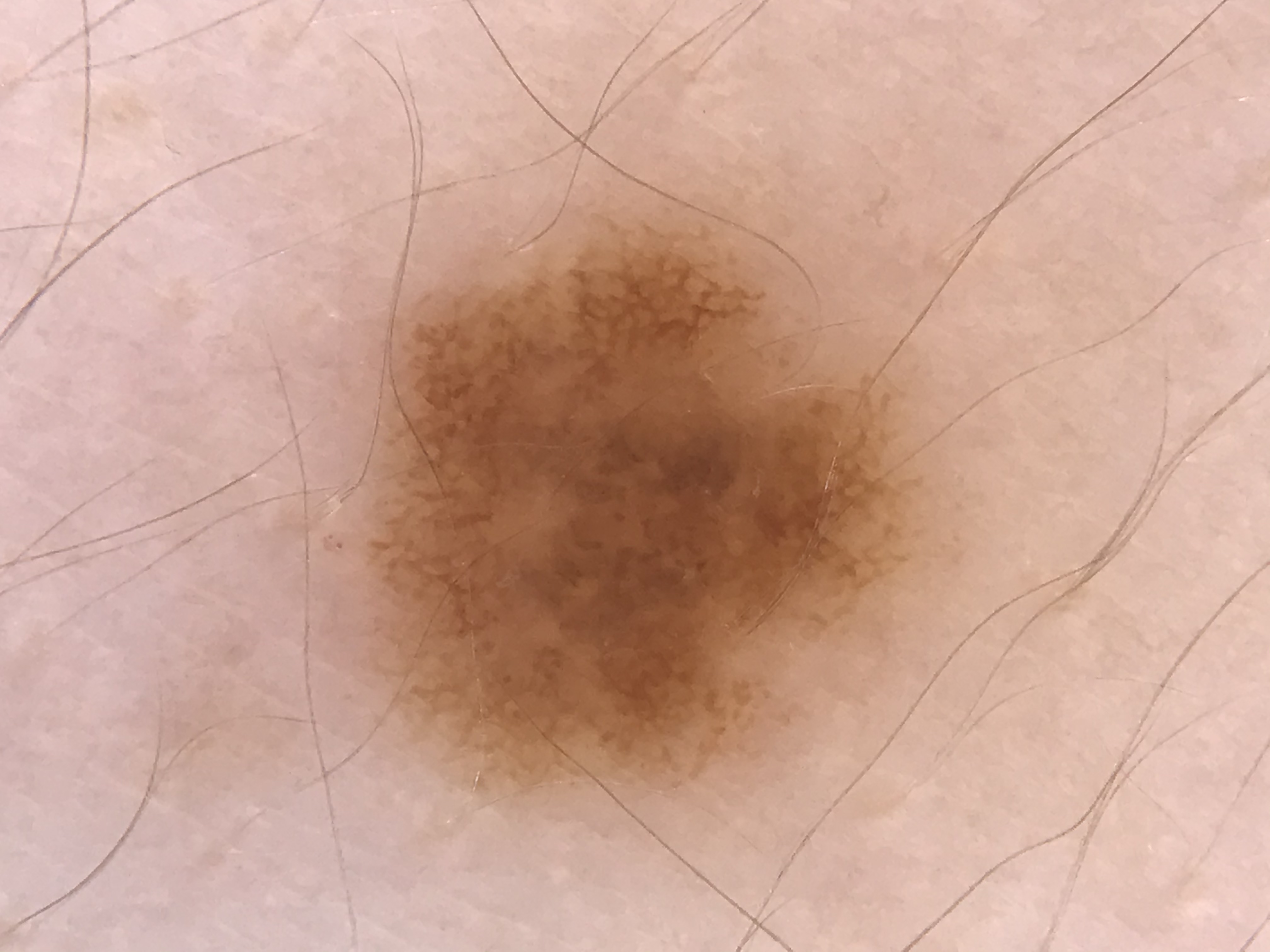Findings:
- imaging — dermatoscopy
- label — dysplastic junctional nevus (expert consensus)